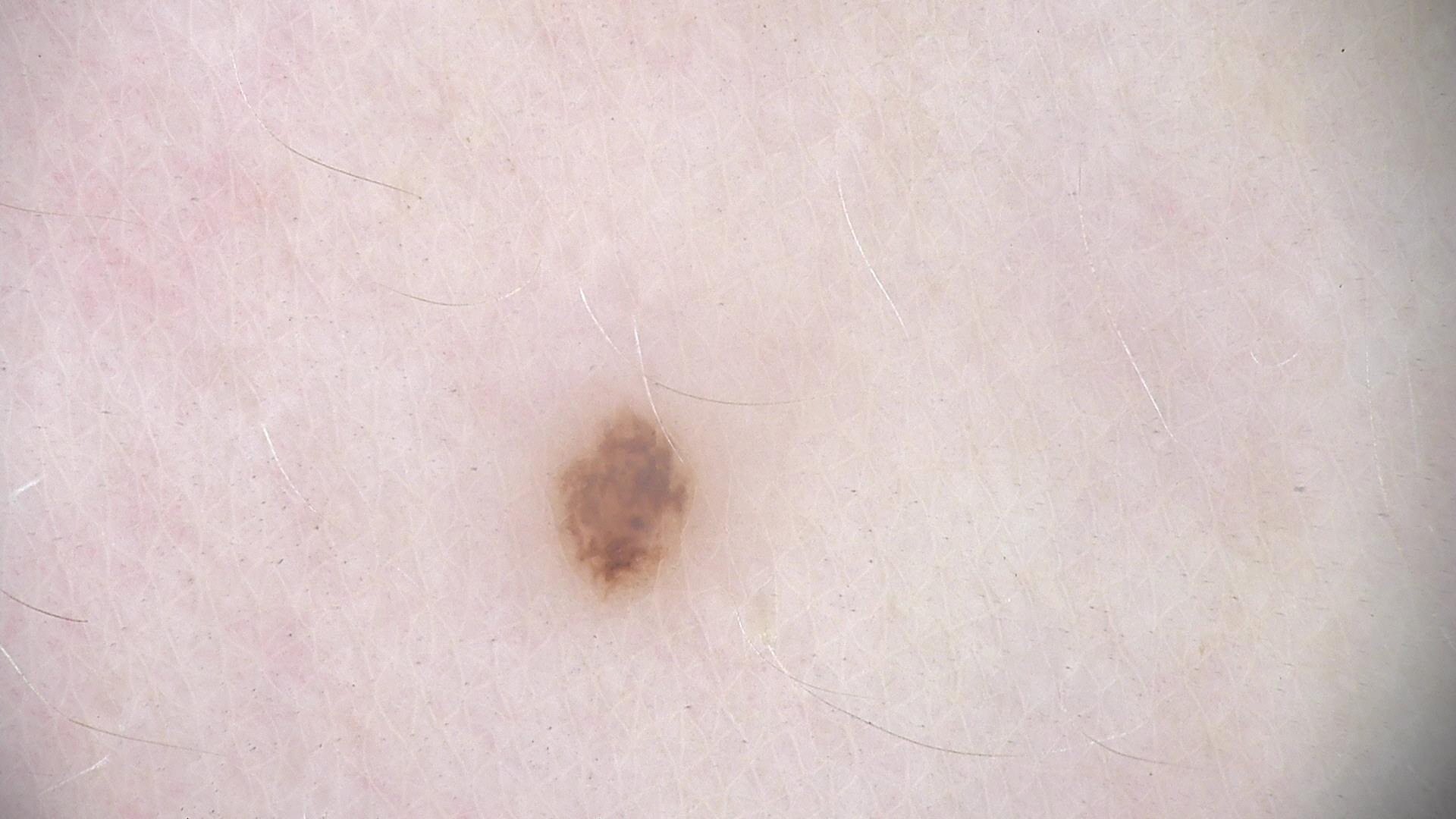| field | value |
|---|---|
| diagnosis | dysplastic junctional nevus (expert consensus) |